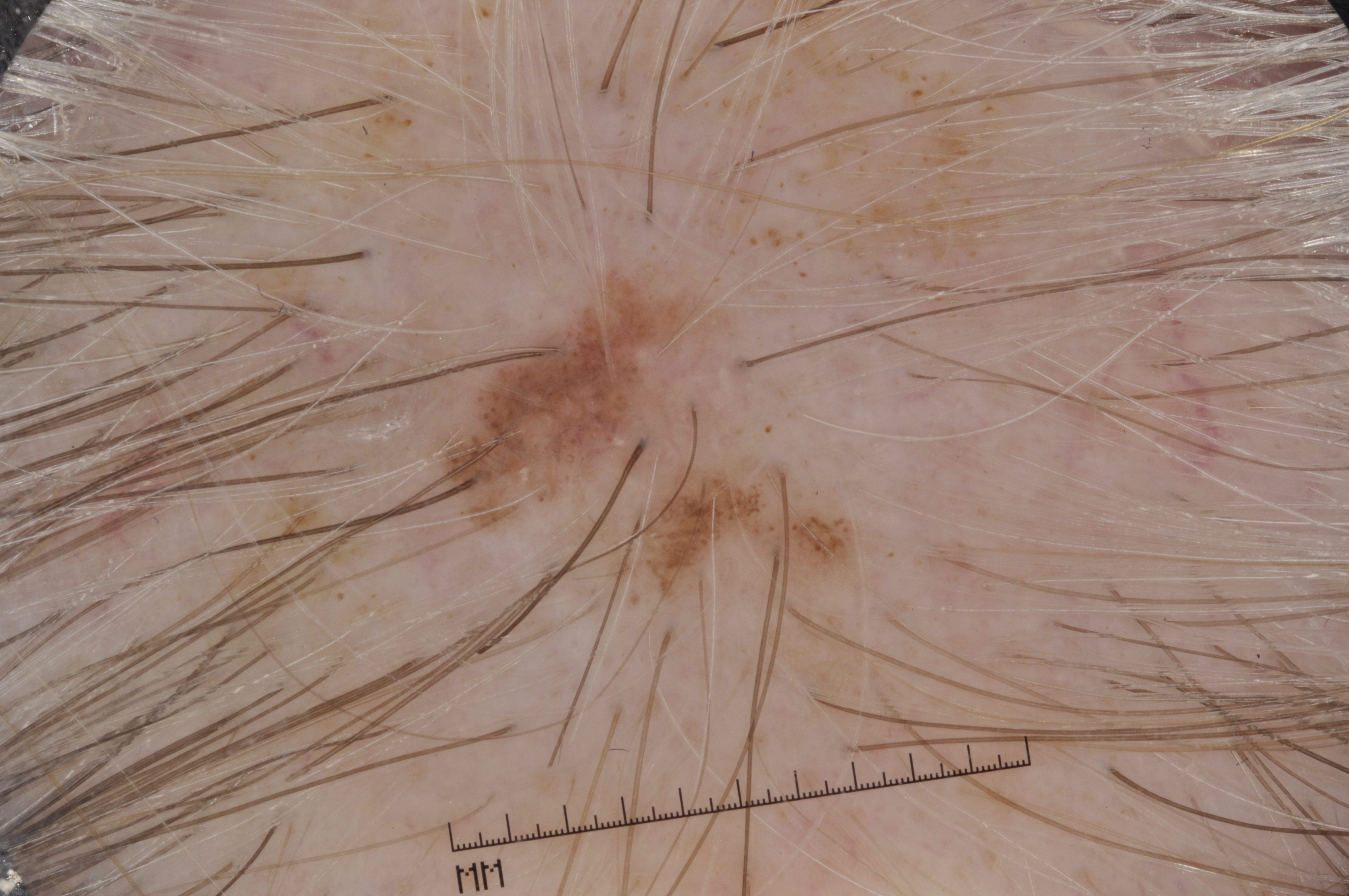Case summary: This is a dermoscopic photograph of a skin lesion. The lesion occupies the region x1=437 y1=254 x2=874 y2=618. The dermoscopic pattern shows no negative network, pigment network, milia-like cysts, or streaks. Conclusion: On biopsy, the diagnosis was a melanoma.